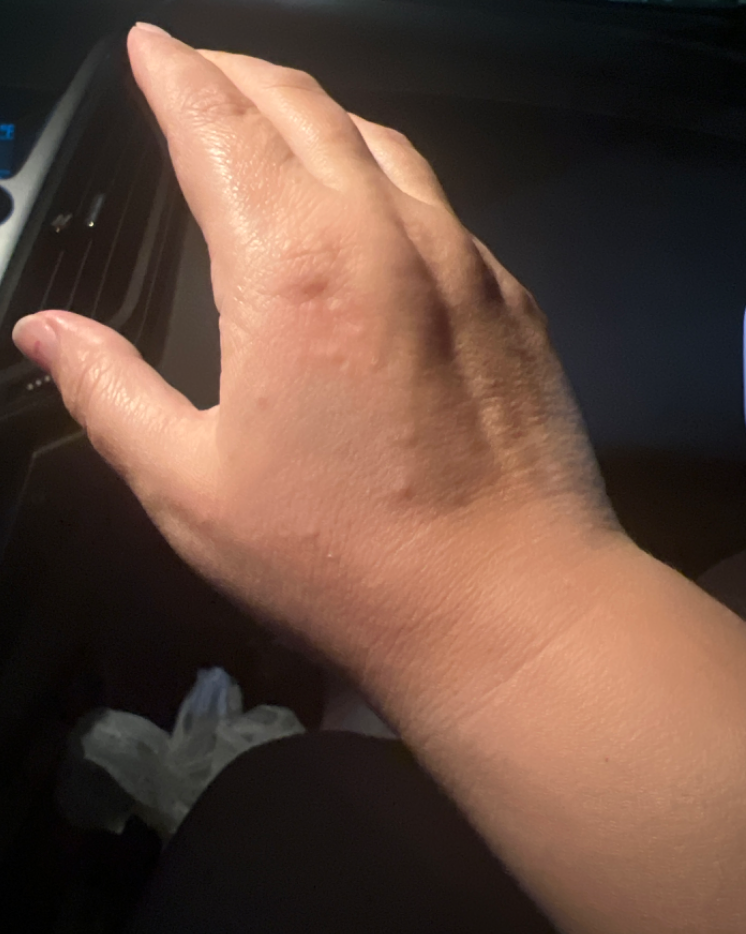The reviewing dermatologist was unable to assign a differential diagnosis from the image. Skin tone: Fitzpatrick phototype III; human graders estimated 2 on the Monk skin tone scale. Texture is reported as raised or bumpy. The patient considered this skin that appeared healthy to them. Located on the back of the hand. The condition has been present for one to four weeks. The photograph was taken at a distance.